A dermoscopic close-up of a skin lesion.
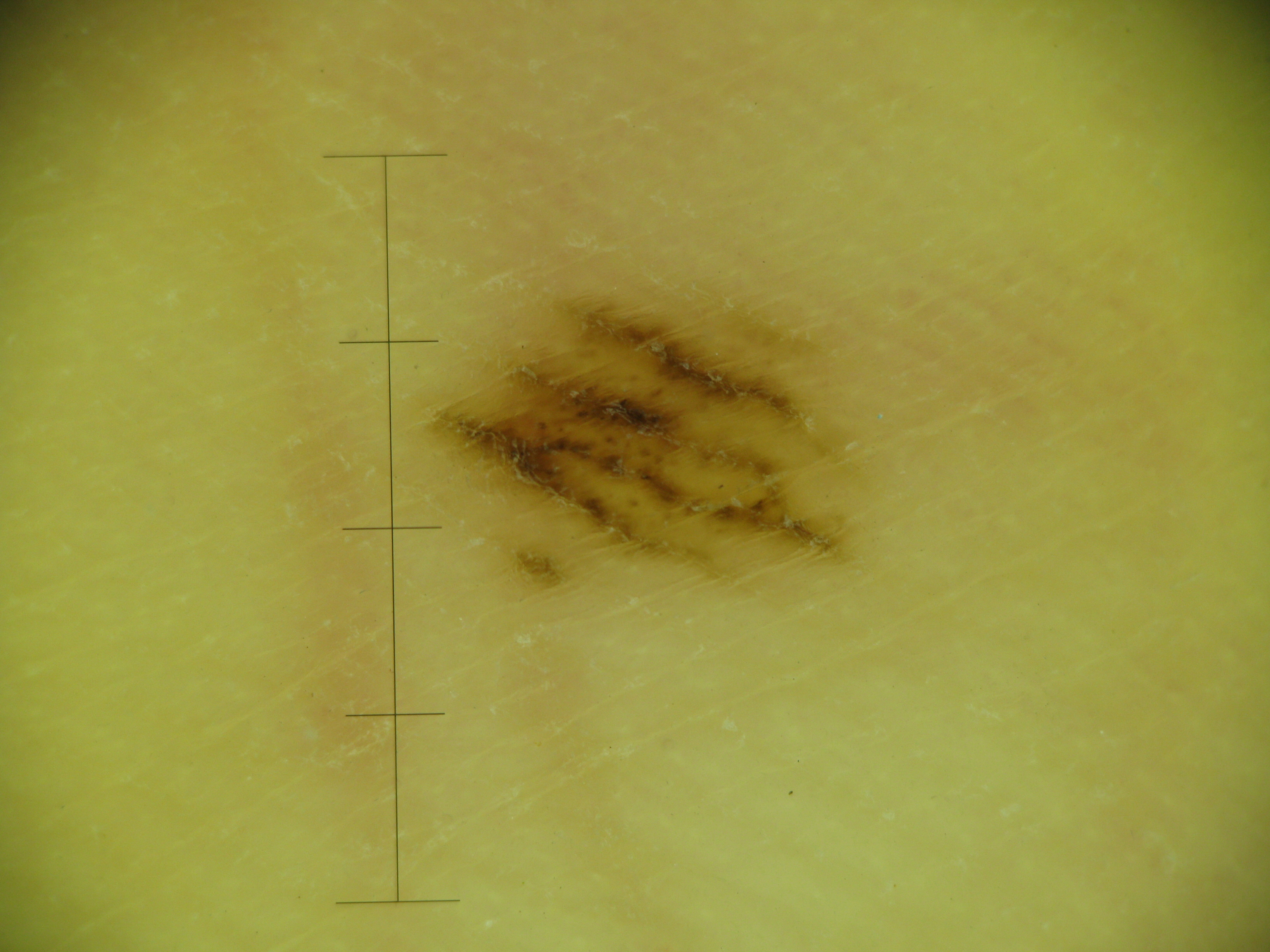Impression: Classified as a banal lesion — an acral junctional nevus.